A dermoscopy image of a single skin lesion:
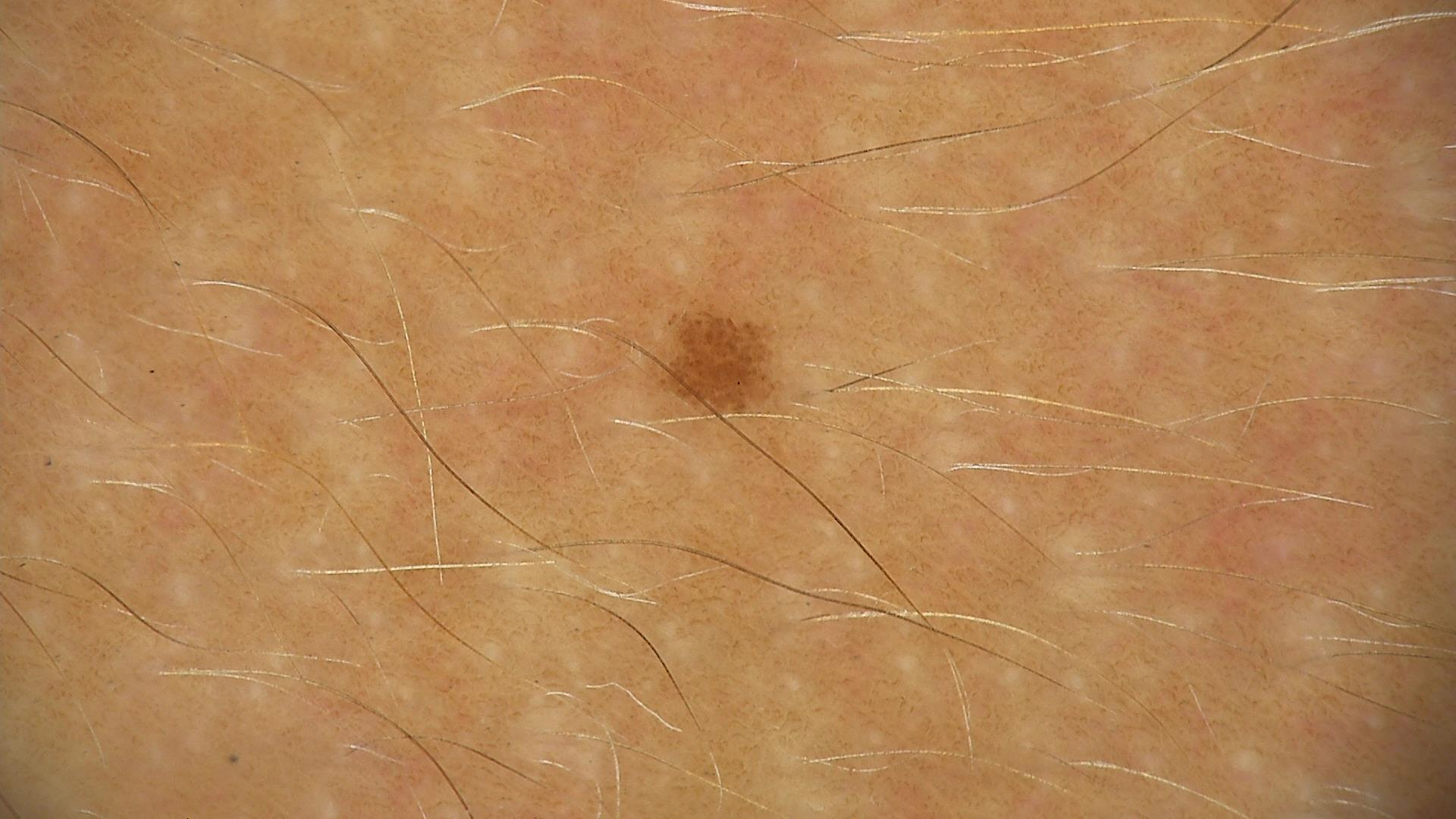label: dysplastic junctional nevus (expert consensus)